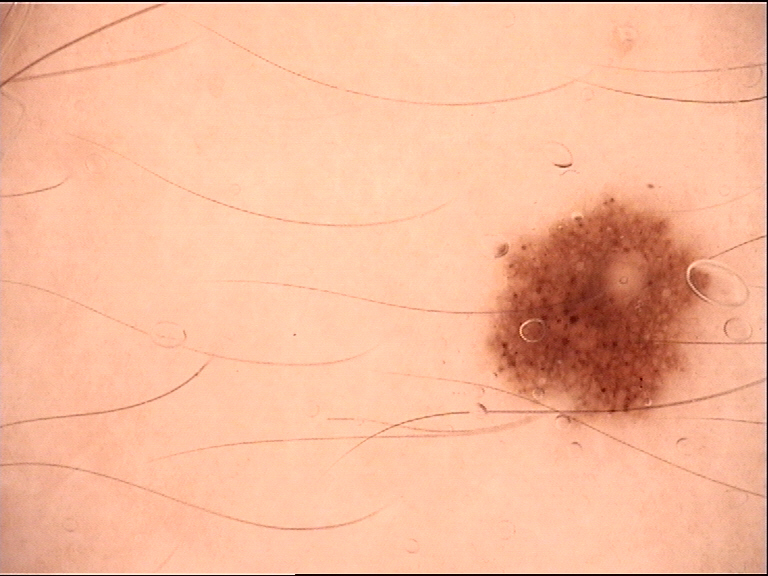assessment: junctional nevus (expert consensus).